A dermoscopic photograph of a skin lesion:
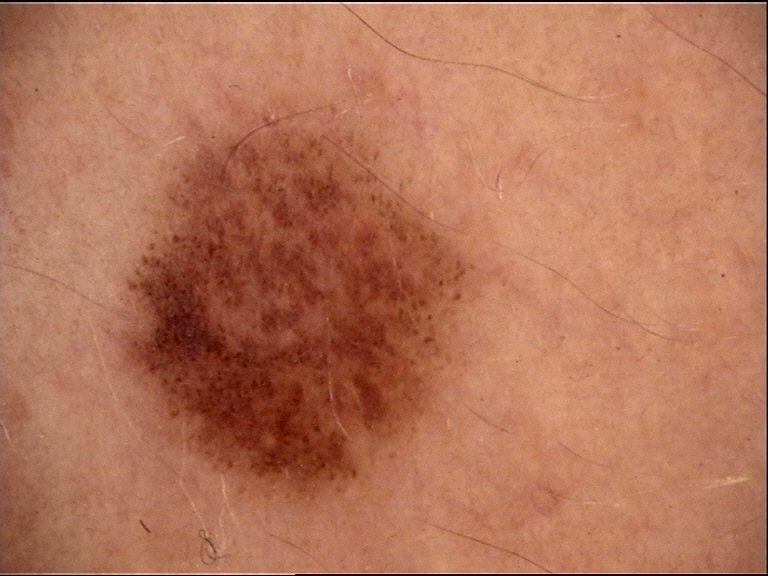Q: What was the diagnostic impression?
A: dysplastic compound nevus (expert consensus)